The subject is a male approximately 70 years of age · a dermoscopic close-up of a skin lesion:
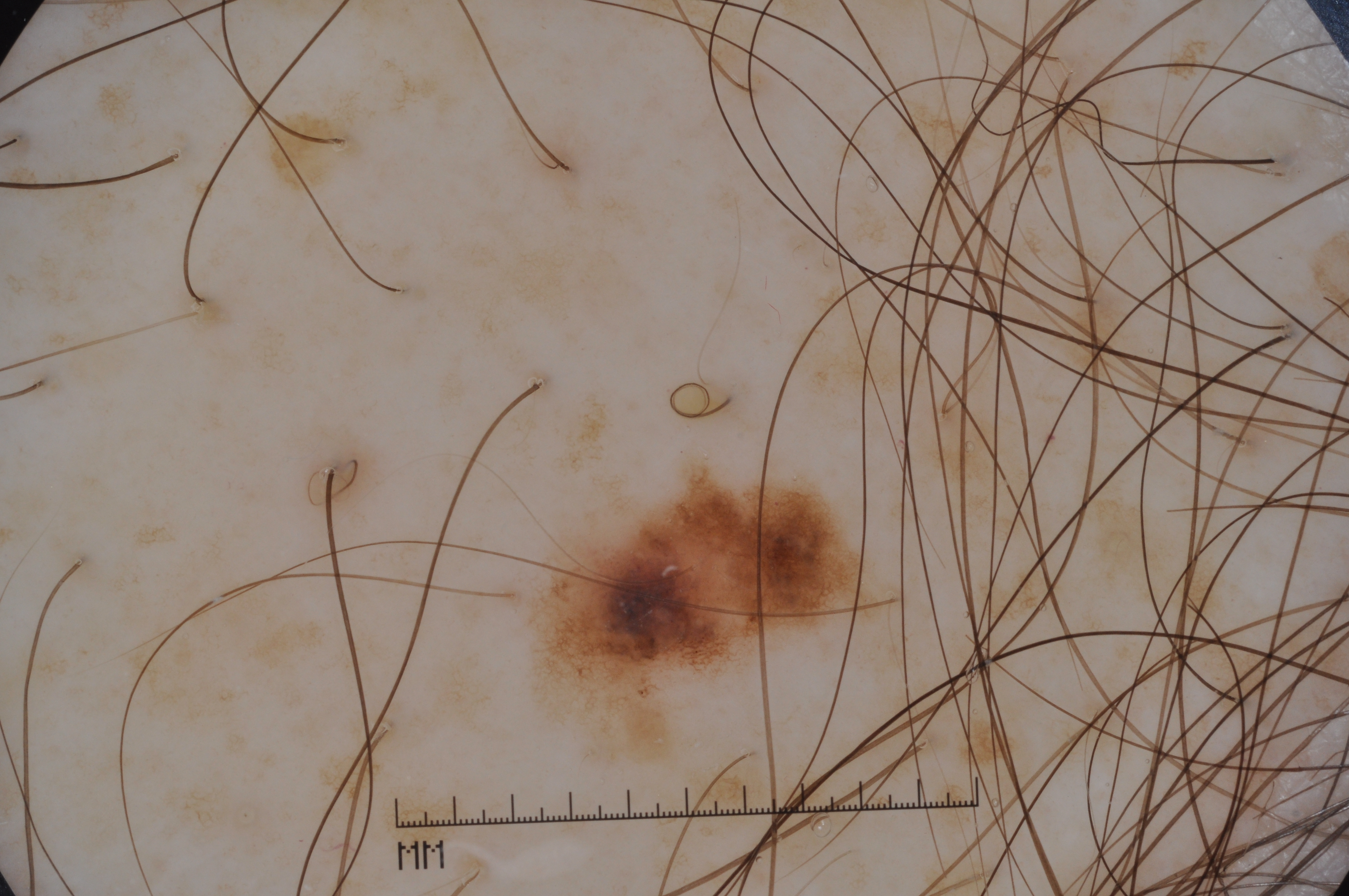The lesion occupies the region x1=548 y1=483 x2=854 y2=693. The lesion occupies roughly 4% of the field. Dermoscopy demonstrates pigment network. Diagnosed as a melanocytic nevus, a benign lesion.